A dermoscopic image of a skin lesion, the subject is a male approximately 60 years of age:
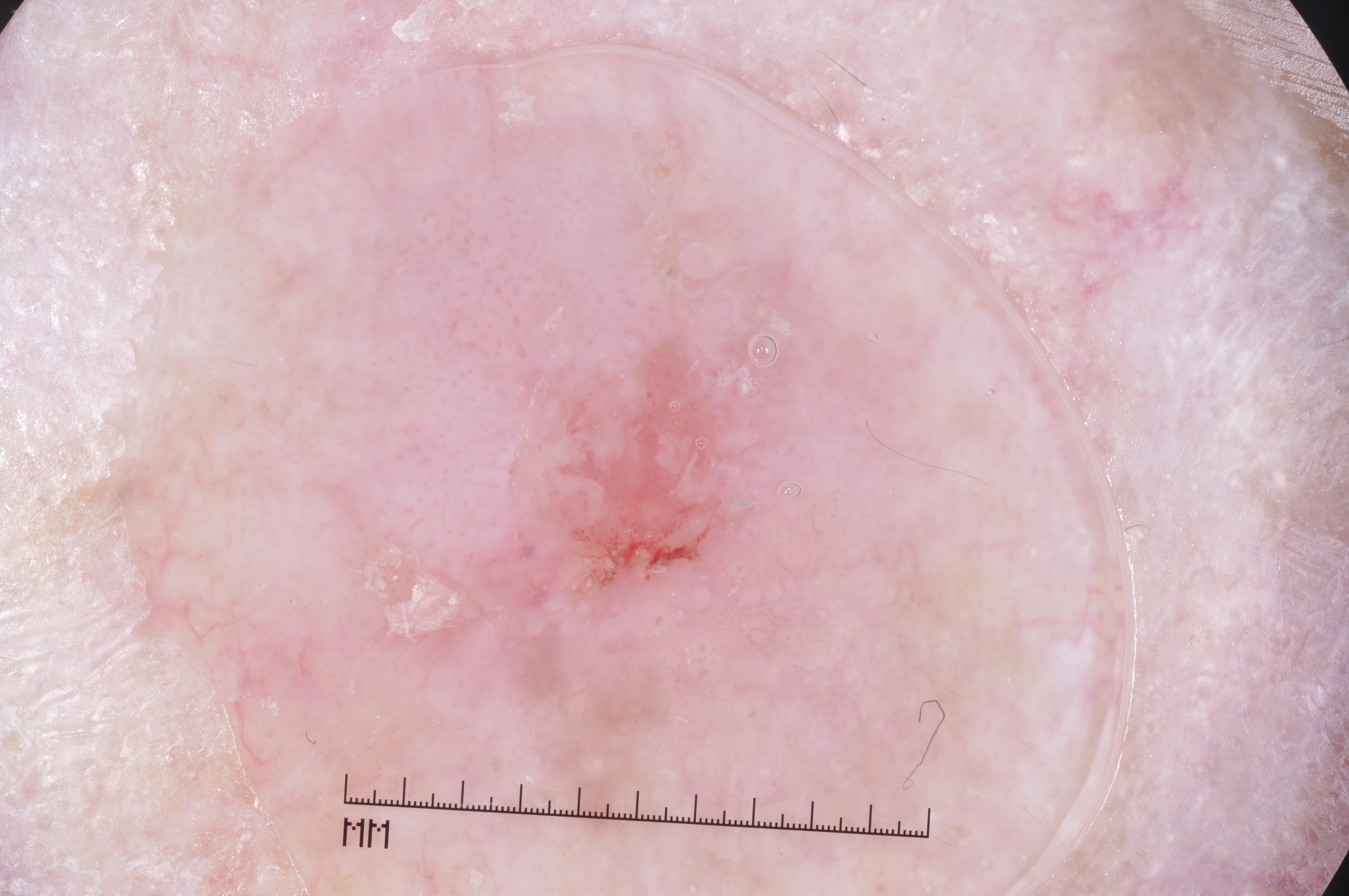<lesion>
<lesion_location>
  <bbox_xyxy>390, 238, 874, 763</bbox_xyxy>
</lesion_location>
<dermoscopic_features>
  <present/>
  <absent>pigment network, negative network, milia-like cysts, streaks</absent>
</dermoscopic_features>
<lesion_extent>moderate</lesion_extent>
<diagnosis>
  <name>seborrheic keratosis</name>
  <malignancy>benign</malignancy>
  <lineage>keratinocytic</lineage>
  <provenance>clinical</provenance>
</diagnosis>
</lesion>